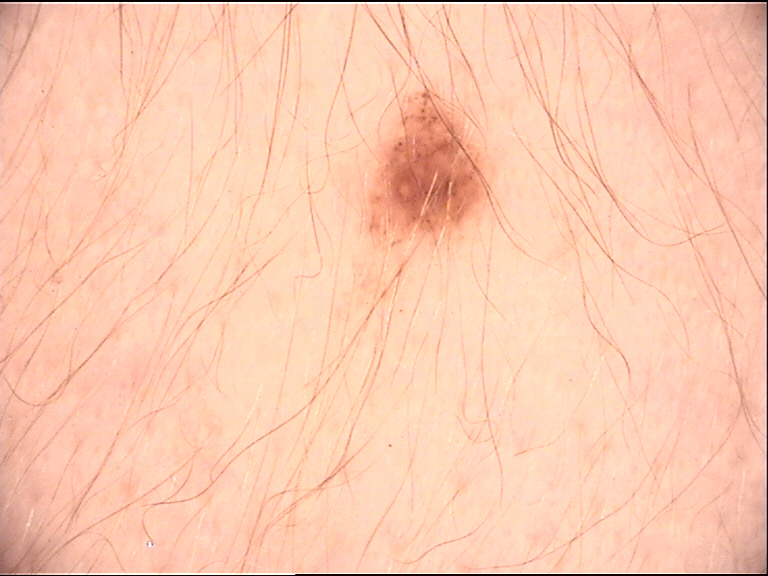Q: What is the imaging modality?
A: dermatoscopy
Q: What is this lesion?
A: junctional nevus (expert consensus)